The photograph is a close-up of the affected area; located on the leg; the patient is 30–39, female.
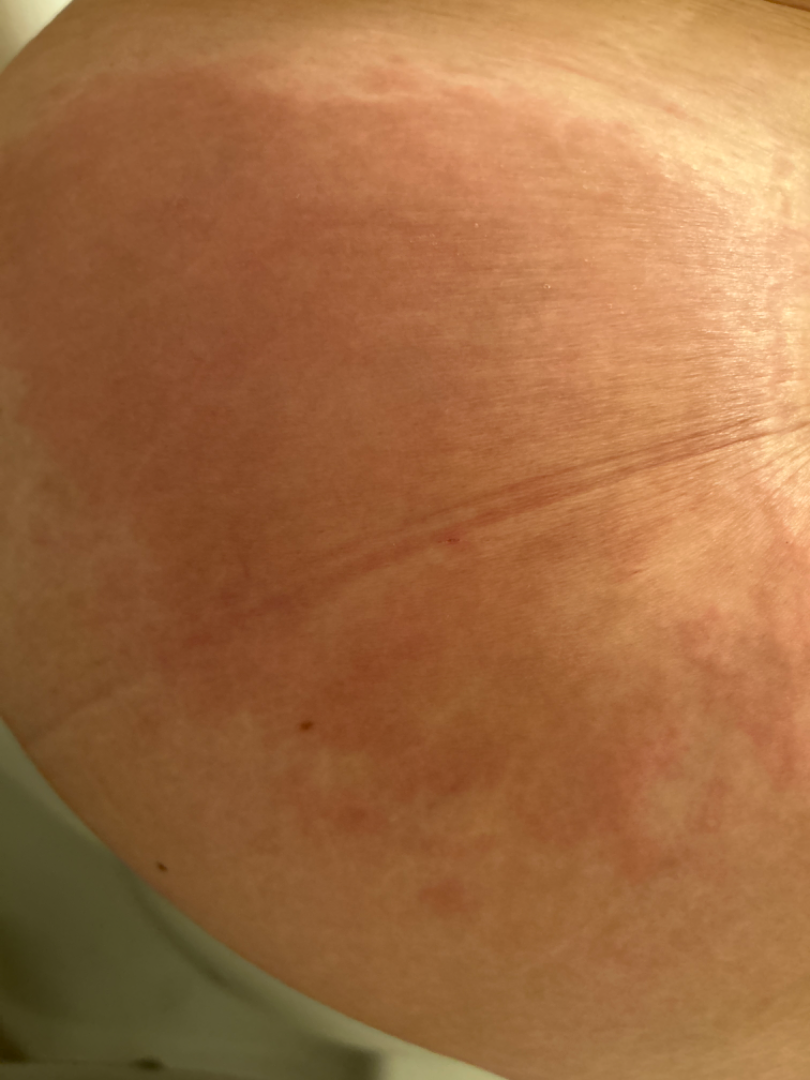The condition has been present for one to four weeks.
Fitzpatrick III.
The lesion is described as flat.
On photographic review by a dermatologist: most consistent with Allergic Contact Dermatitis.